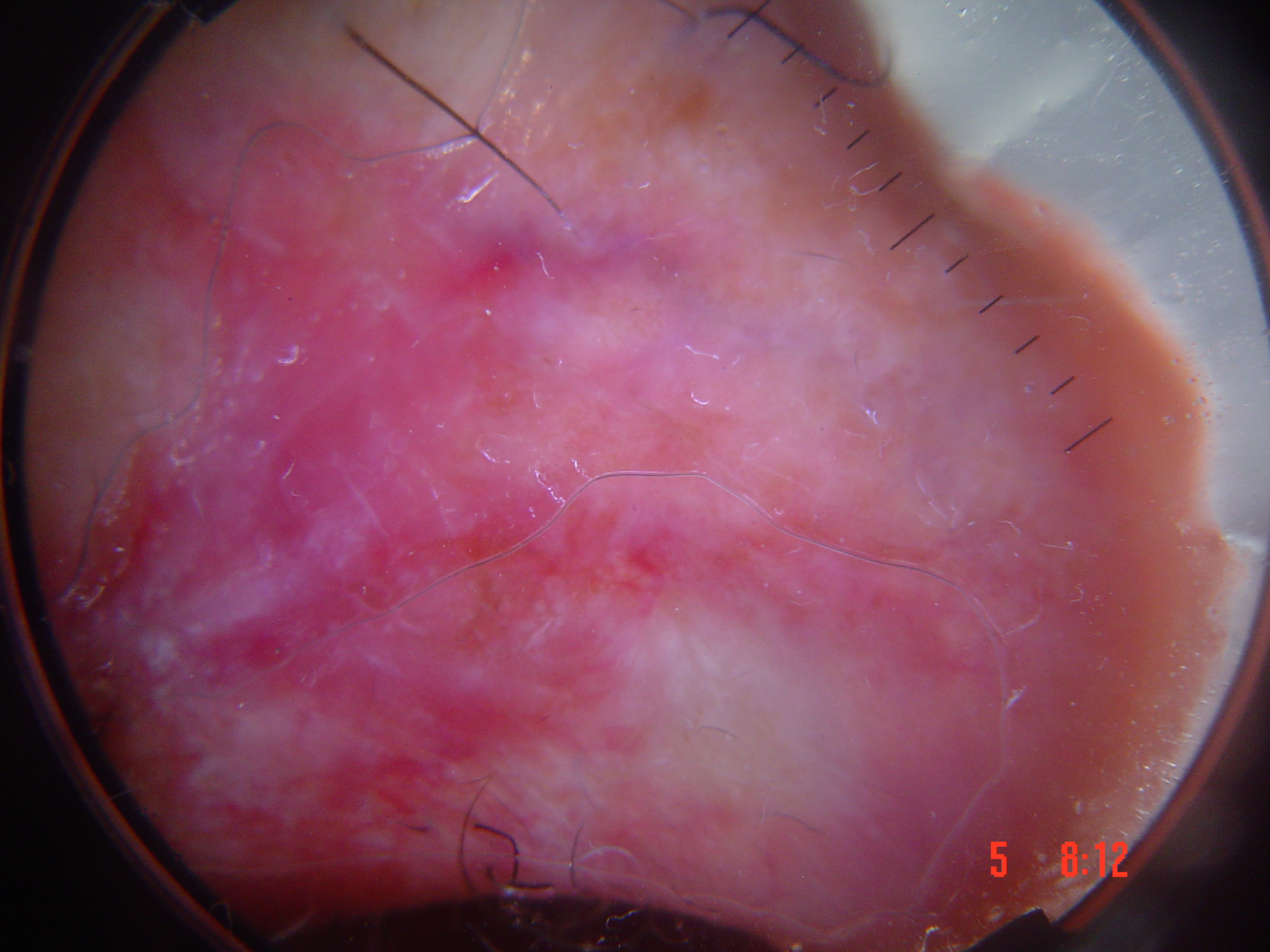Confirmed on histopathology as a basal cell carcinoma.